The chart notes a first-degree relative with melanoma. Recorded as FST III. Contact-polarized dermoscopy of a skin lesion. A male patient roughly 40 years of age — 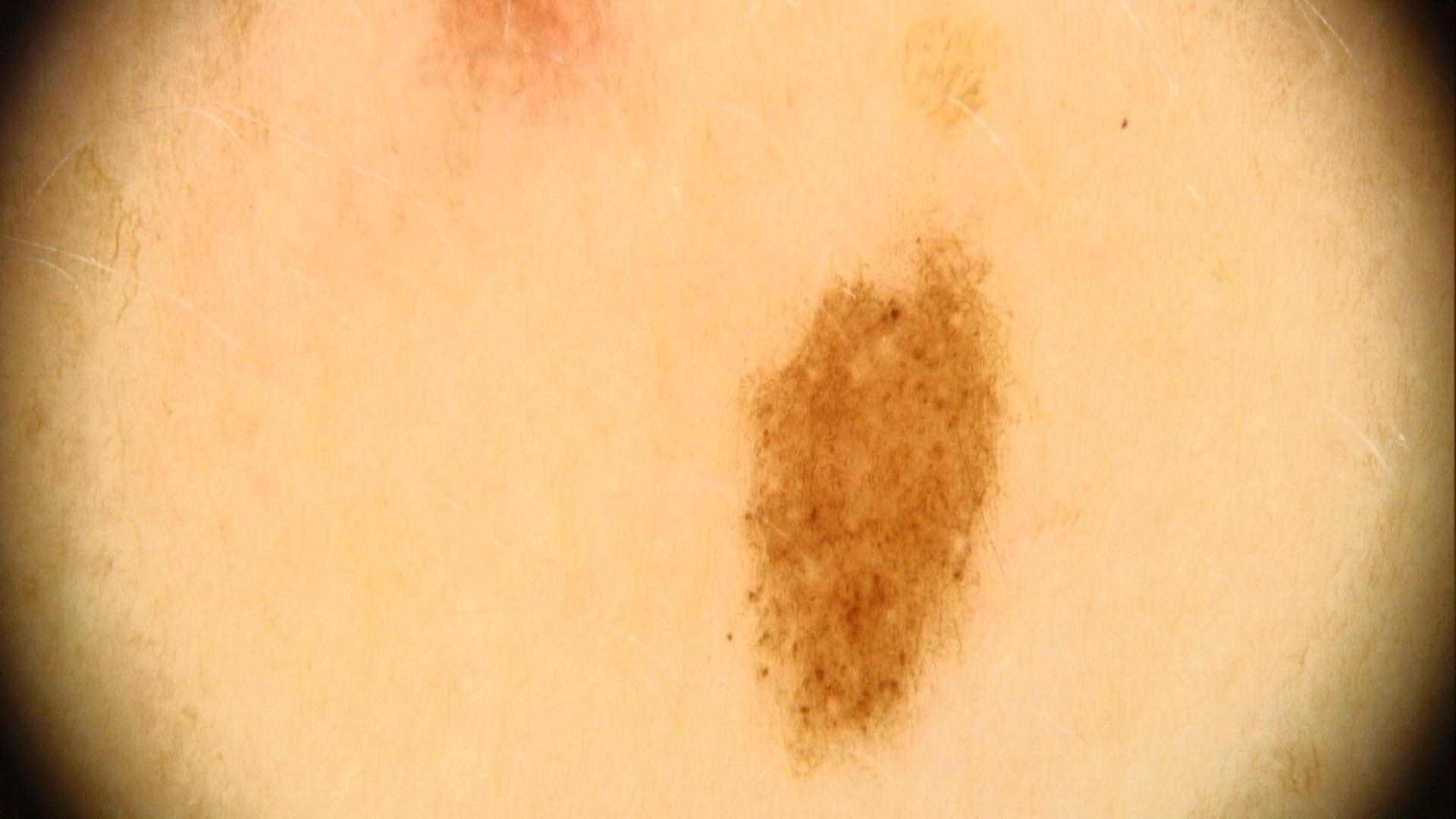Findings:
The lesion involves the posterior trunk.
Conclusion:
The diagnostic impression was a nevus.